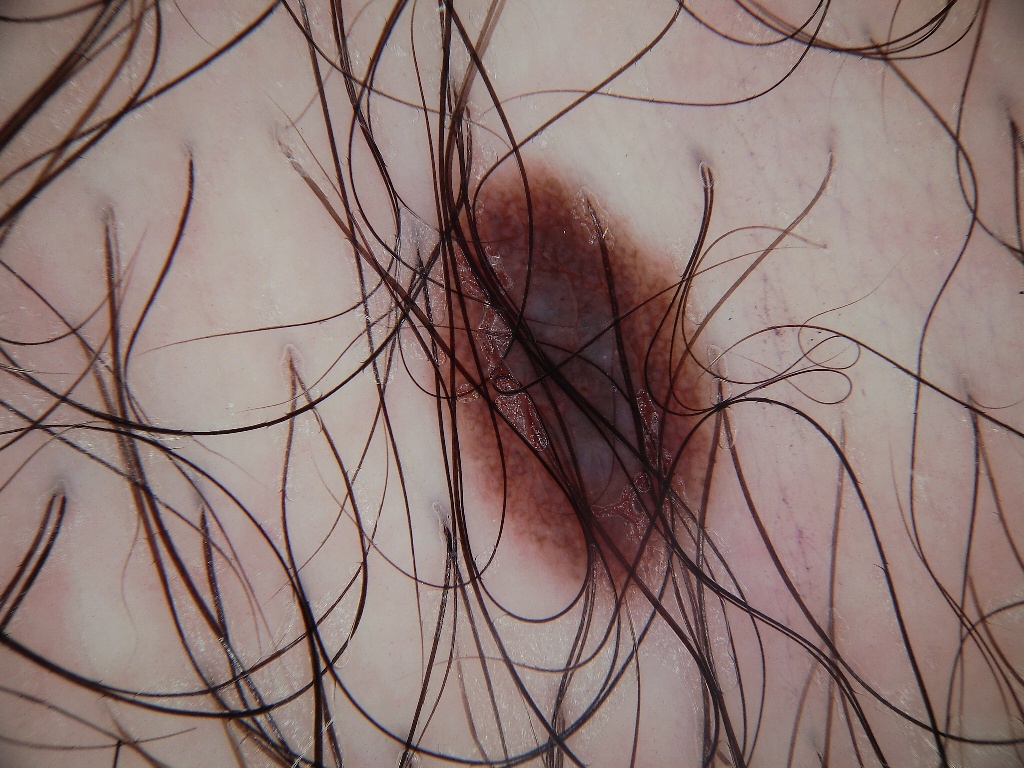Findings:
A dermoscopic image of a skin lesion. The lesion takes up about 13% of the image. The lesion occupies the region x1=432, y1=159, x2=722, y2=616.
Conclusion:
The lesion was assessed as a benign lesion.